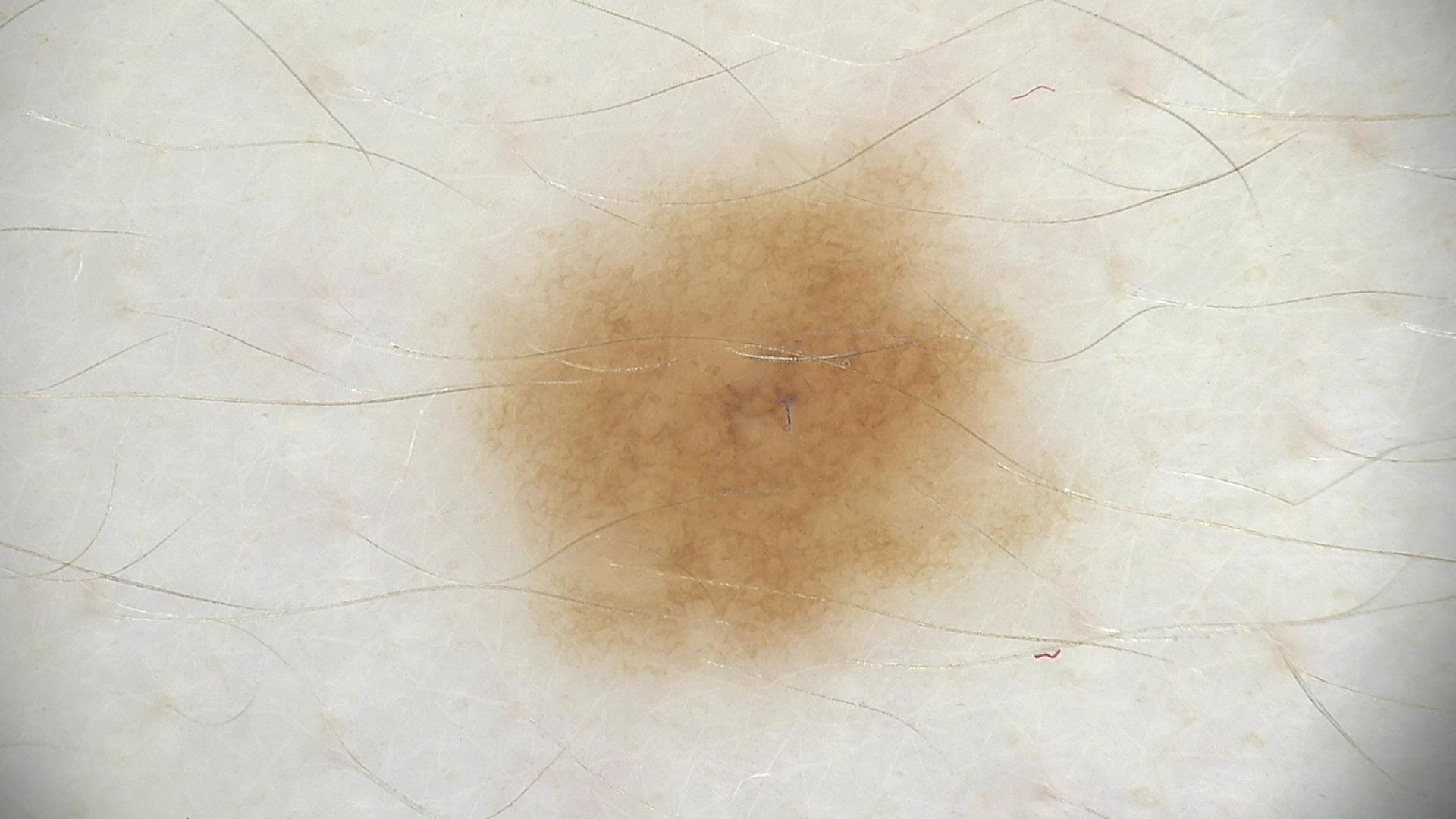  image: dermoscopy
  diagnosis:
    name: dysplastic junctional nevus
    code: jd
    malignancy: benign
    super_class: melanocytic
    confirmation: expert consensus